A dermoscopic image of a skin lesion.
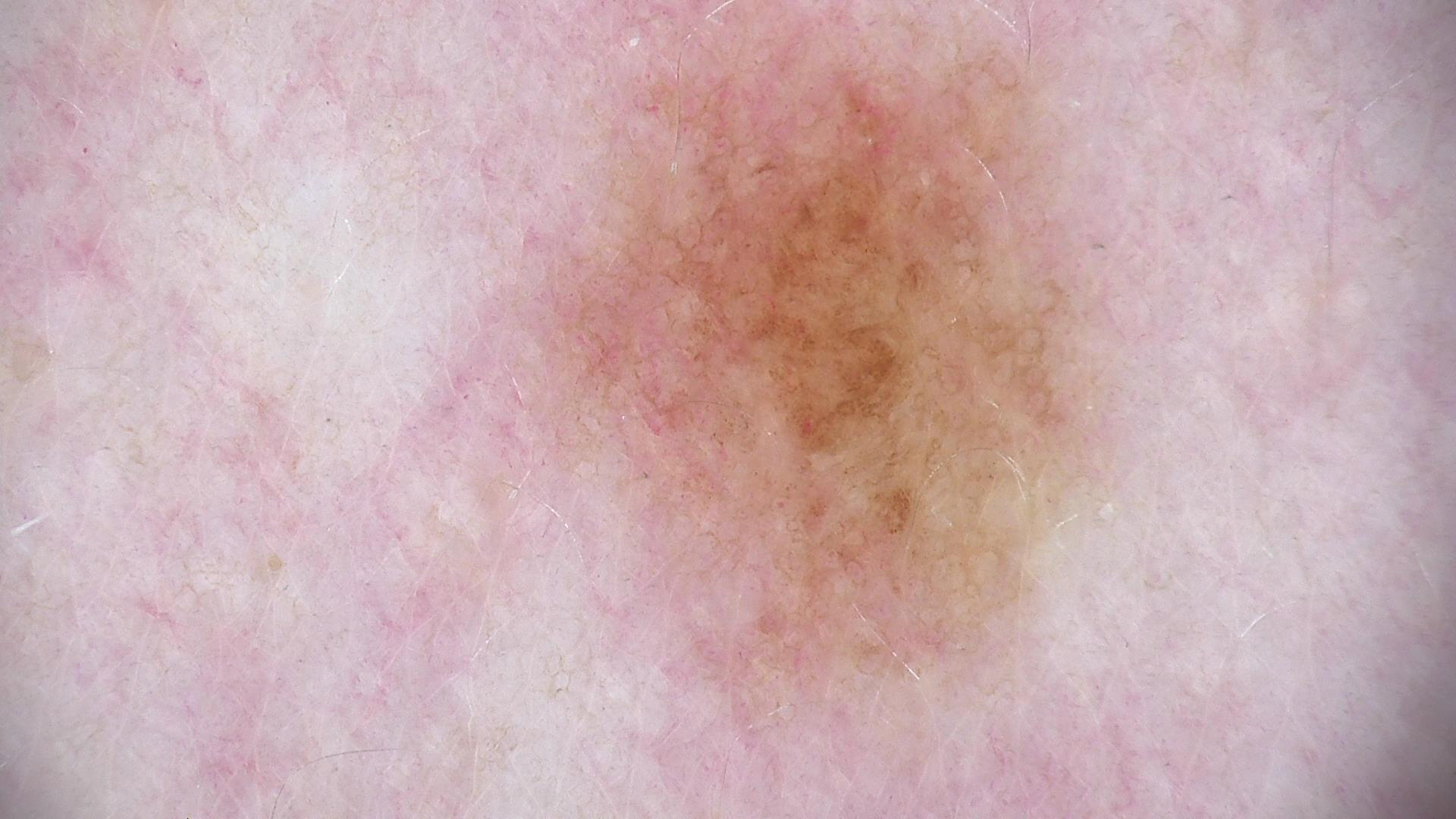Impression: Classified as a dysplastic junctional nevus.